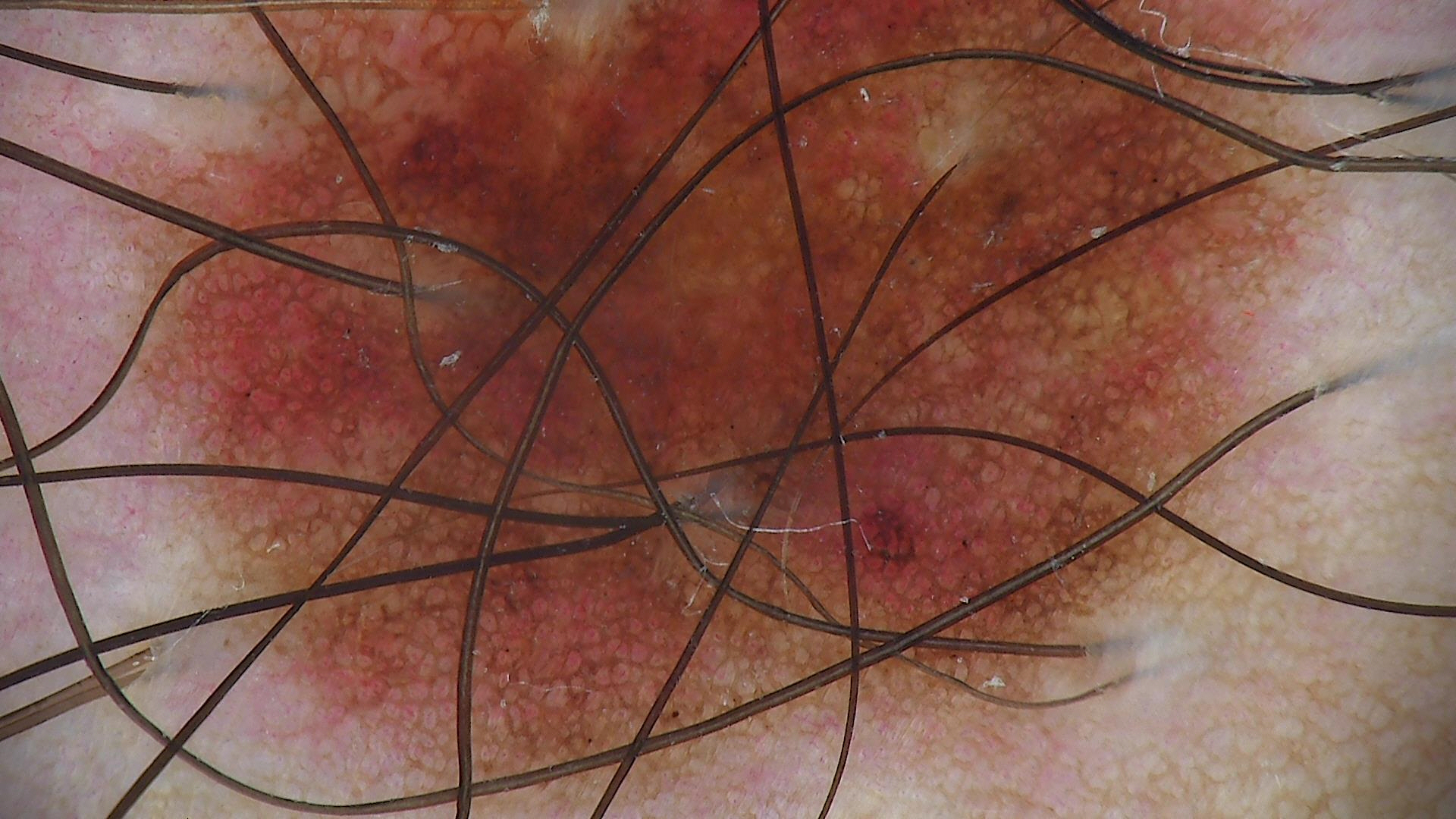| field | value |
|---|---|
| image | dermatoscopy |
| diagnostic label | dysplastic junctional nevus (expert consensus) |